A dermoscopic image of a skin lesion: 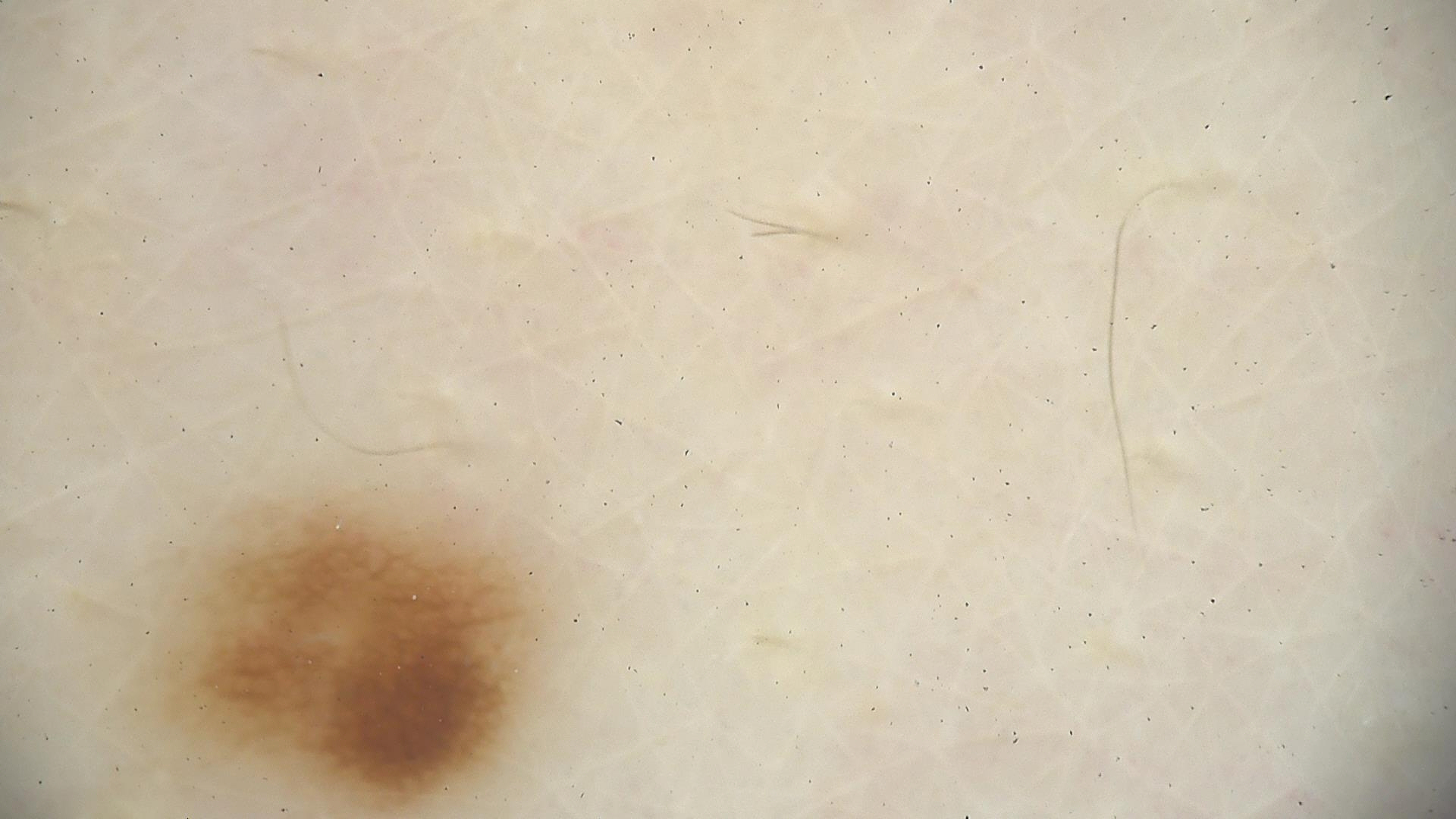{"diagnosis": {"name": "dysplastic junctional nevus", "code": "jd", "malignancy": "benign", "super_class": "melanocytic", "confirmation": "expert consensus"}}